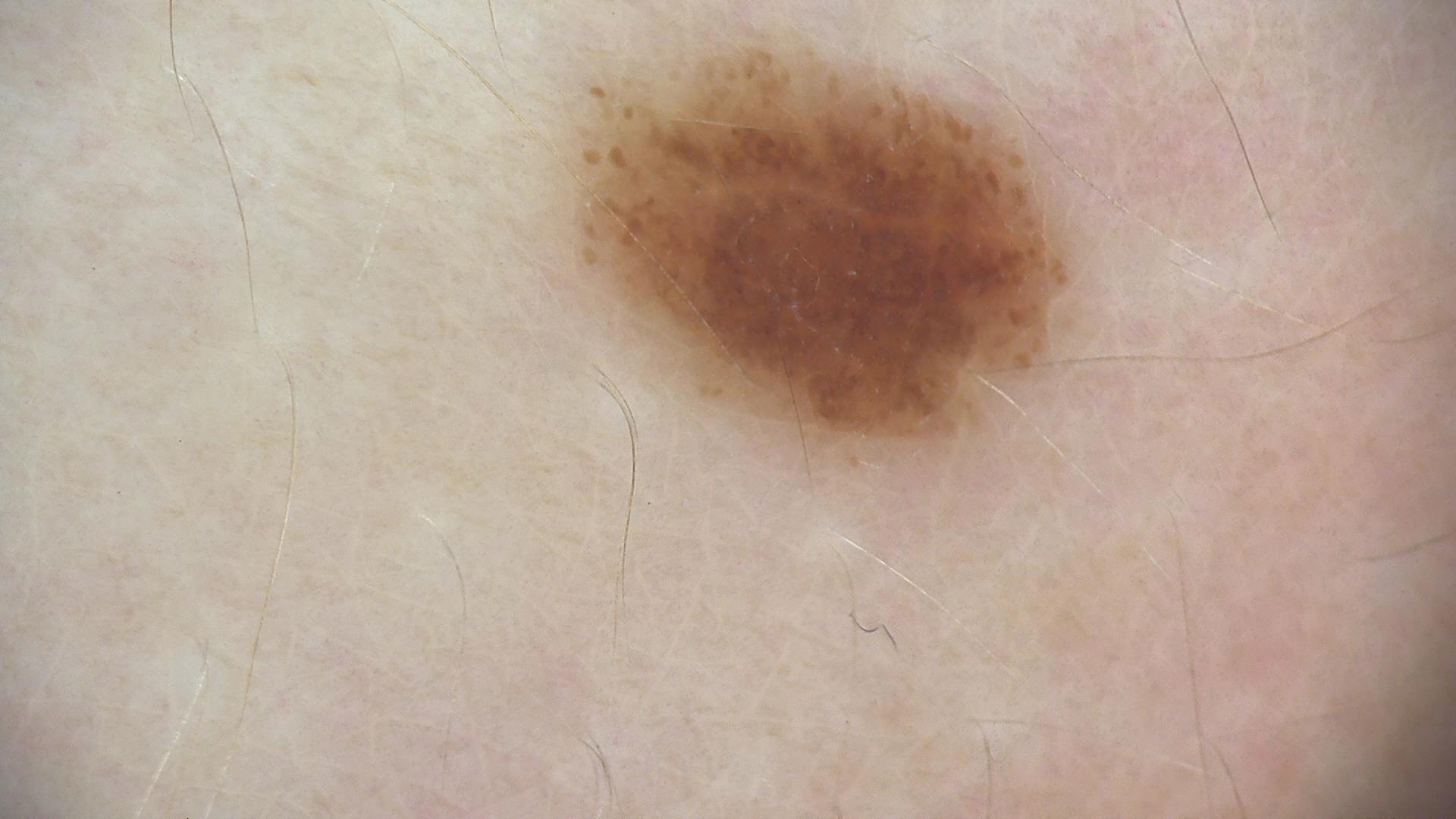class = dysplastic junctional nevus (expert consensus)